An image taken at an angle:
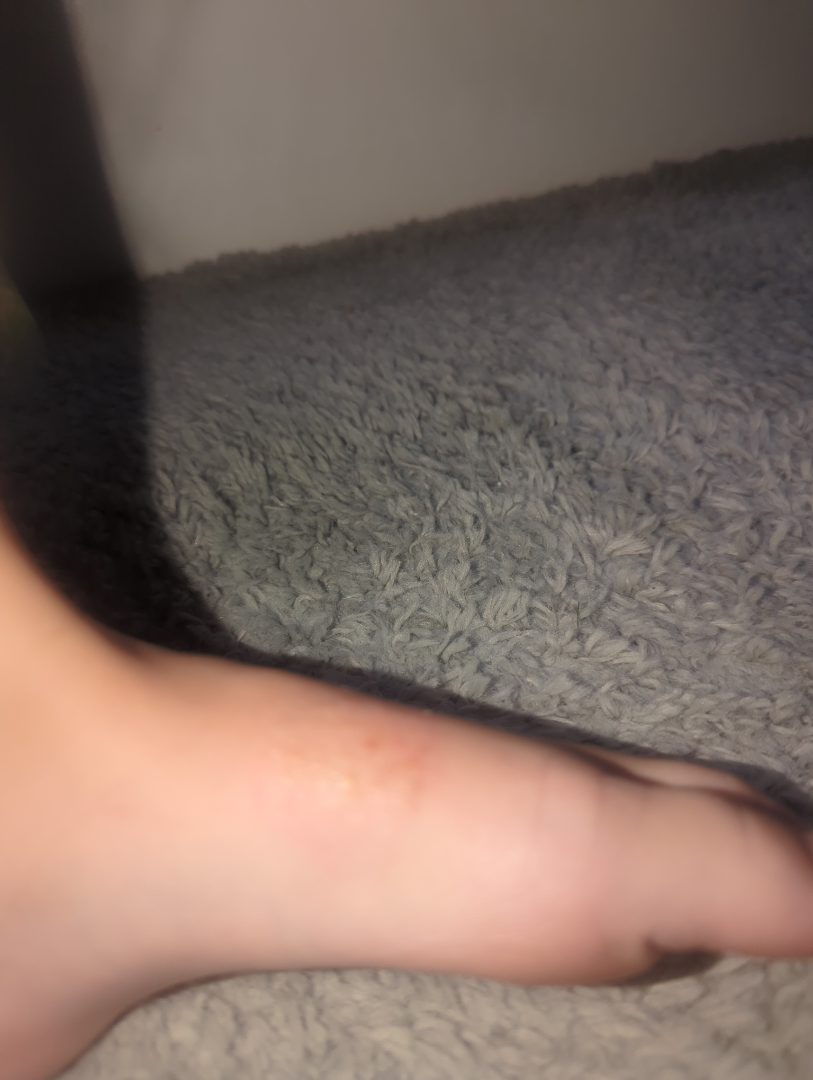Notes:
• differential diagnosis · Eczema and Allergic Contact Dermatitis were each considered, in no particular order